The lesion is described as raised or bumpy; the patient described the issue as a rash; the condition has been present for about one day; the arm is involved; no associated systemic symptoms reported; reported lesion symptoms include itching; the photo was captured at a distance: 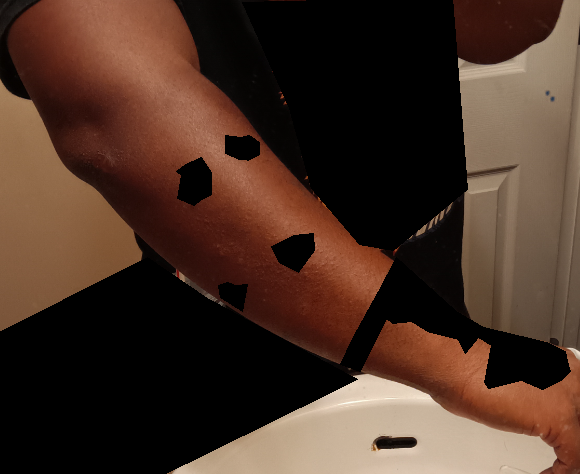Findings:
- assessment · Lichen spinulosus (41%); Eczema (41%); Keratosis pilaris (18%)